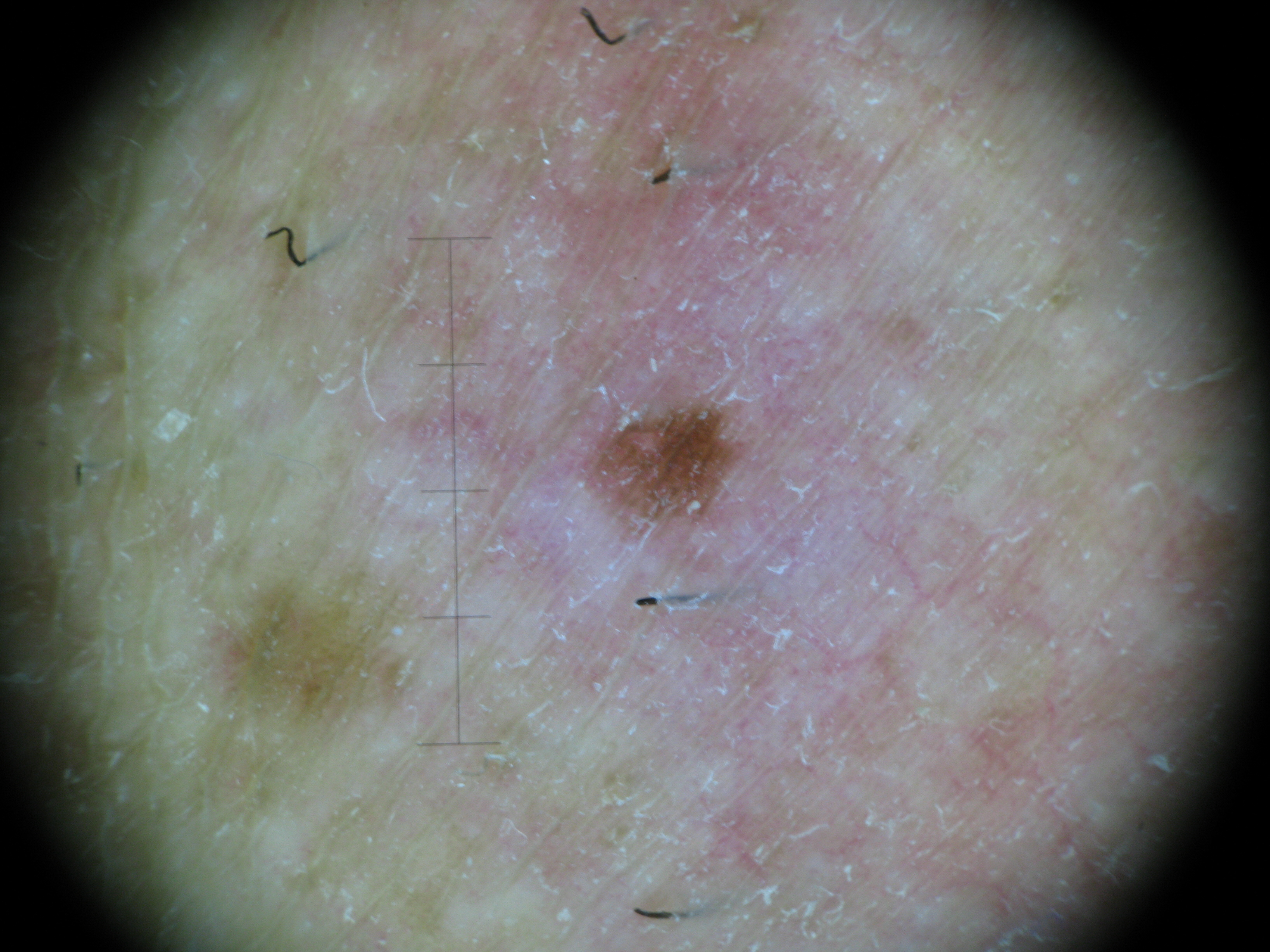{
  "diagnosis": {
    "name": "dysplastic junctional nevus",
    "code": "jd",
    "malignancy": "benign",
    "super_class": "melanocytic",
    "confirmation": "expert consensus"
  }
}